This is a close-up image · the lesion involves the back of the hand, head or neck, back of the torso and arm · the patient also reports shortness of breath, mouth sores, fatigue, chills and joint pain · the condition has been present for more than one year · reported lesion symptoms include bothersome appearance, itching, burning, darkening and pain · texture is reported as raised or bumpy and fluid-filled · the contributor is a female aged 30–39 — 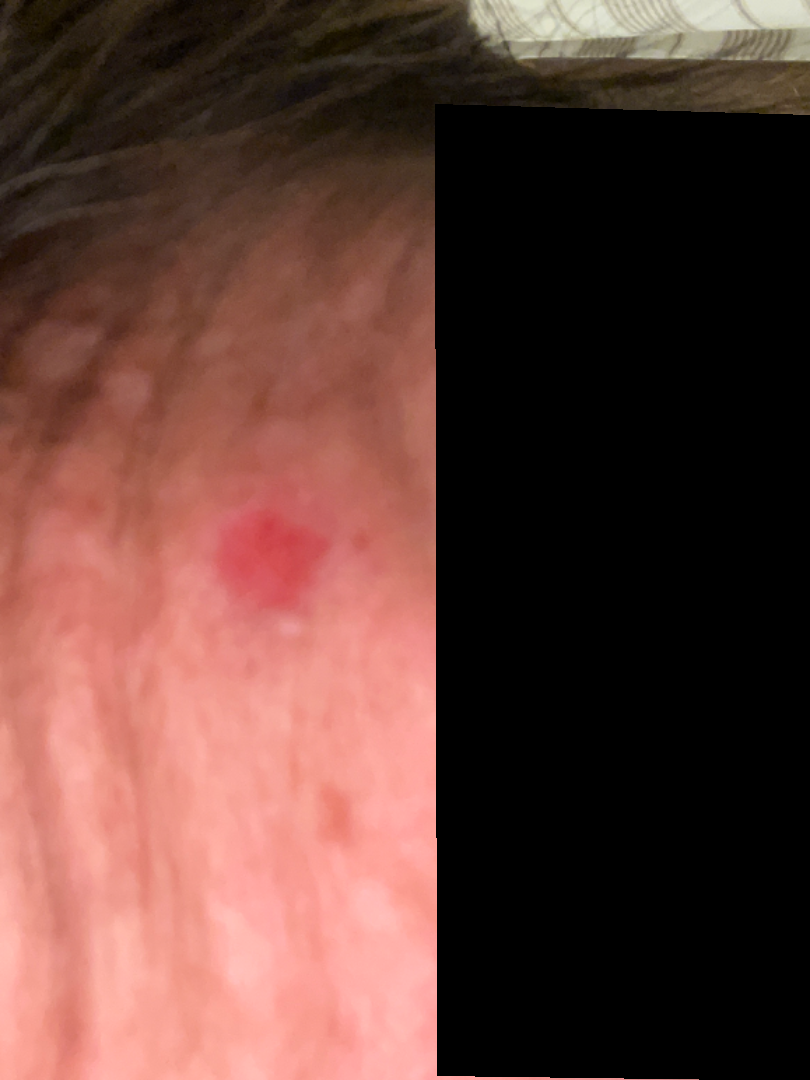- dermatologist impression: Basal Cell Carcinoma (primary); Traumatic ulcer (possible)